The subject is a male approximately 60 years of age. A dermoscopic view of a skin lesion.
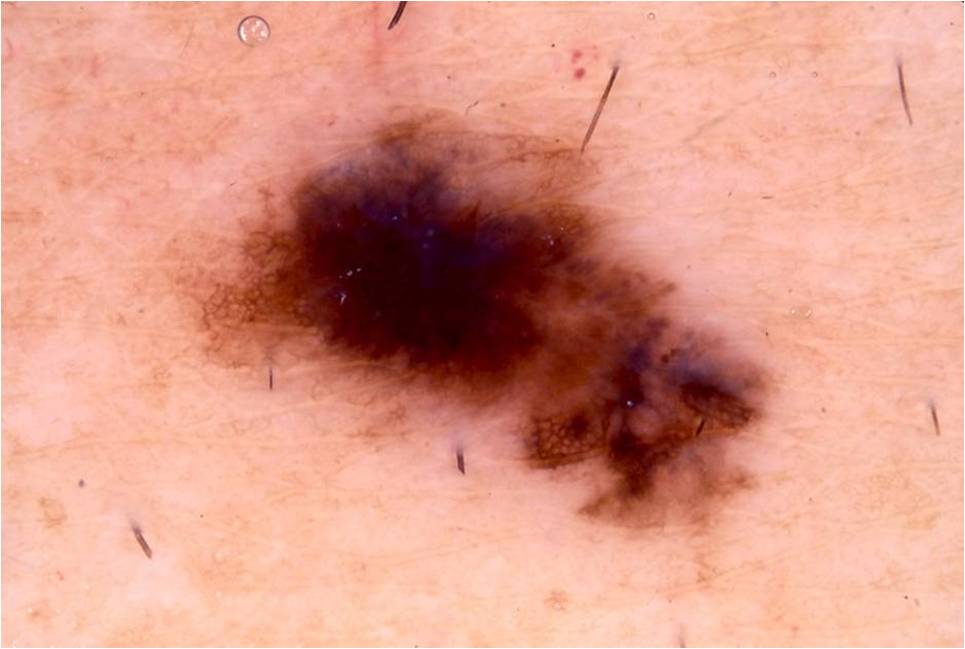Case summary:
* dermoscopic findings · pigment network and globules; absent: milia-like cysts, negative network, and streaks
* lesion bbox · x1=178, y1=106, x2=797, y2=550
* lesion extent · moderate
* assessment · a melanoma, a malignancy